Recorded as Fitzpatrick skin type III. A female subject aged 77. A clinical photograph of a skin lesion — 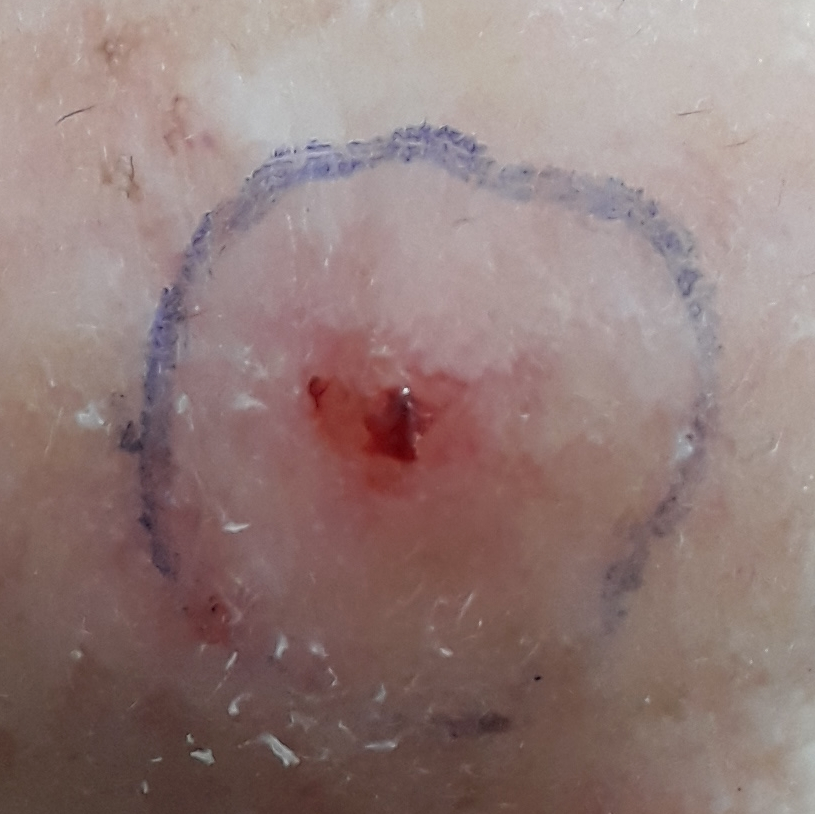{
  "lesion_size": {
    "diameter_1_mm": 4.0,
    "diameter_2_mm": 3.0
  },
  "diagnosis": {
    "name": "basal cell carcinoma",
    "code": "BCC",
    "malignancy": "malignant",
    "confirmation": "histopathology"
  }
}